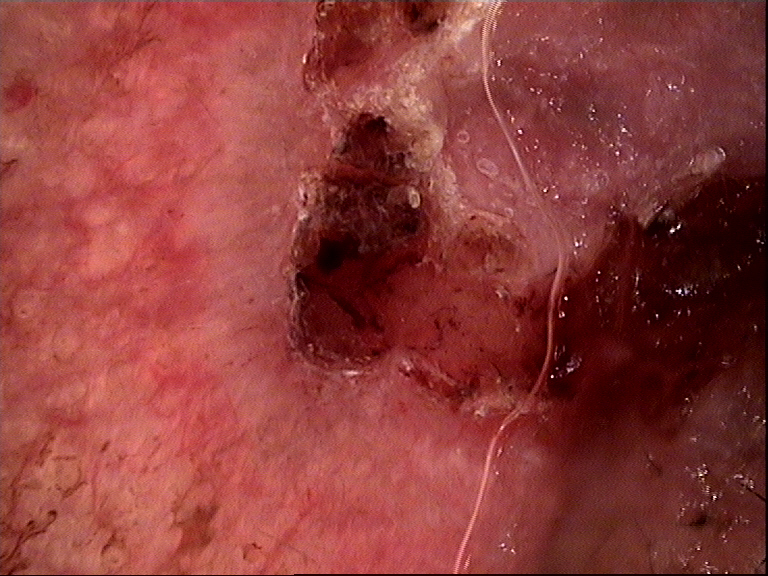Q: What is the diagnosis?
A: basal cell carcinoma (biopsy-proven)